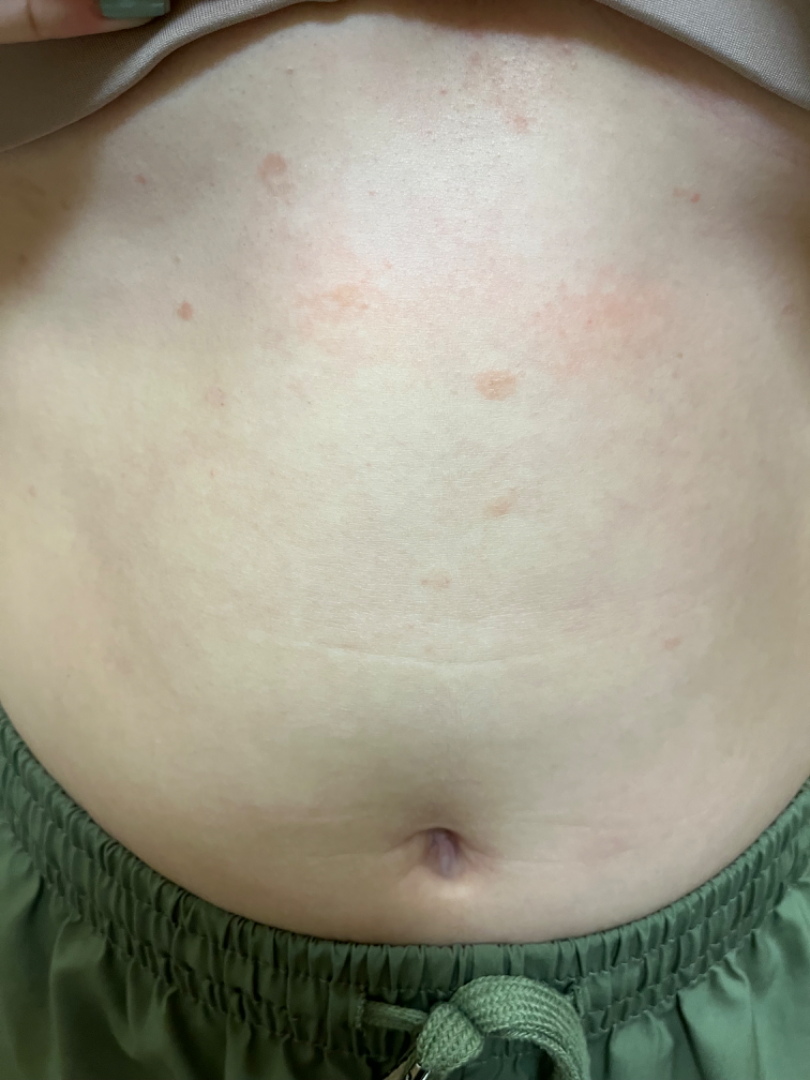diagnostic considerations=Pityriasis rosea and Acute and chronic dermatitis were considered with similar weight.